The lesion involves the arm, the photograph was taken at an angle, the lesion is associated with itching and bothersome appearance, the lesion is described as flat, skin tone: Fitzpatrick II; non-clinician graders estimated Monk skin tone scale 1–2 — 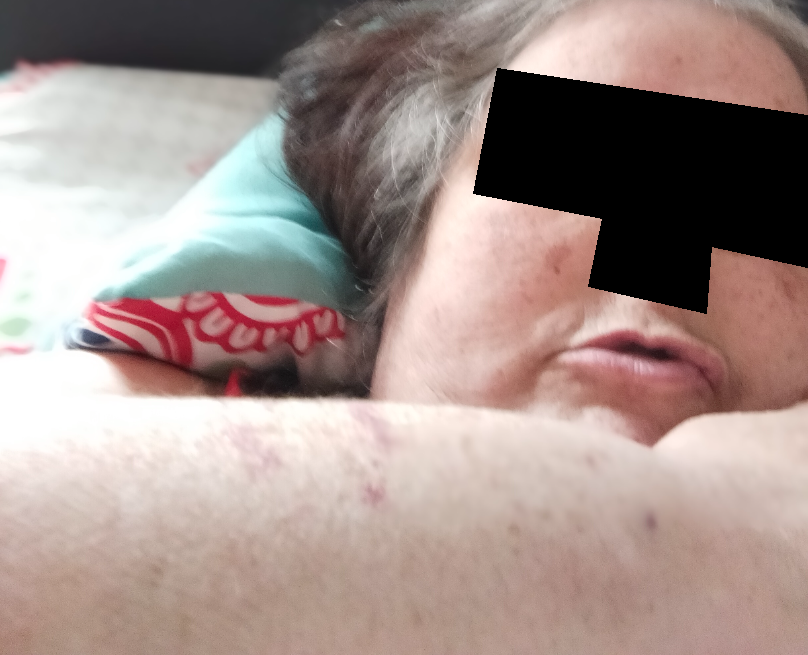Q: Could the case be diagnosed?
A: indeterminate from the photograph